A dermoscopic view of a skin lesion:
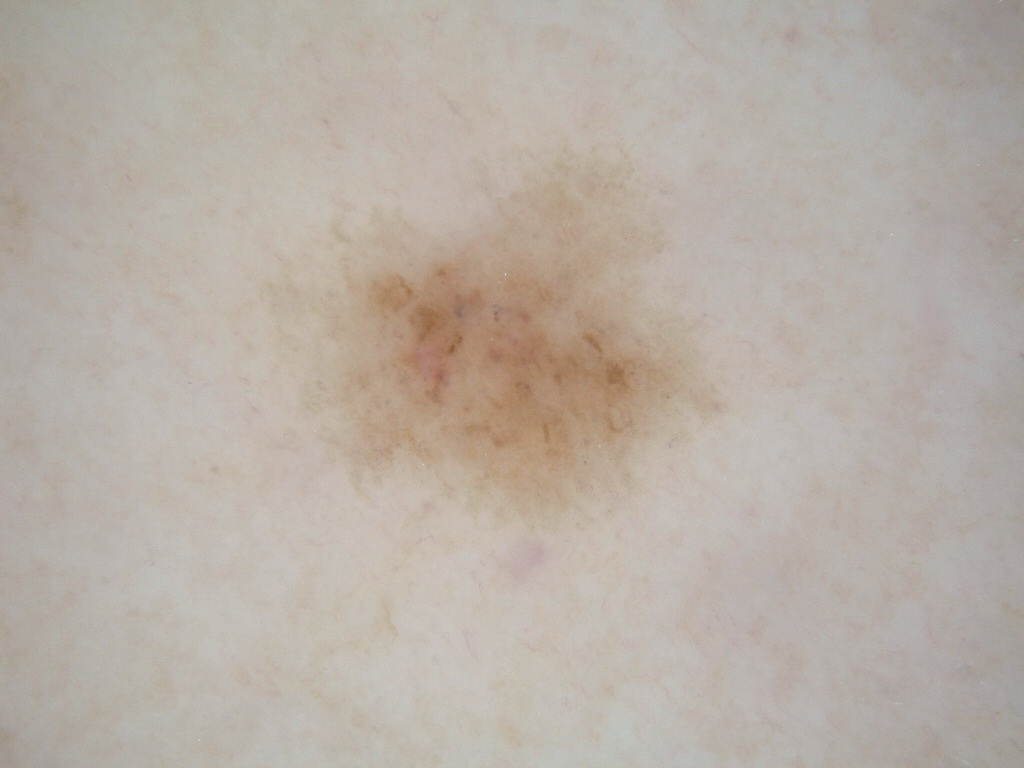lesion_location:
  bbox_xyxy:
    - 264
    - 142
    - 722
    - 526
diagnosis:
  name: melanocytic nevus
  malignancy: benign
  lineage: melanocytic
  provenance: clinical